A dermatoscopic image of a skin lesion.
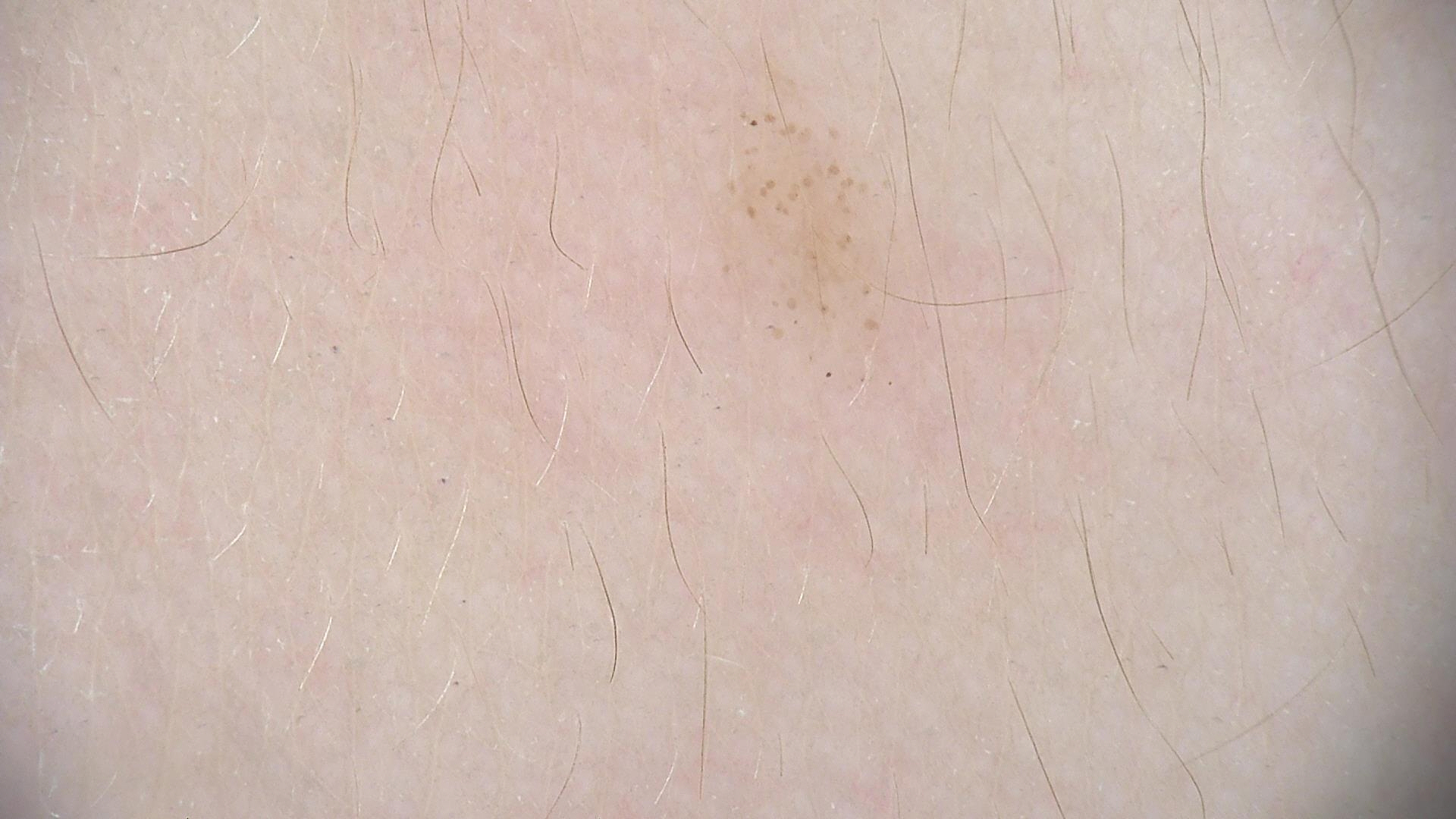Labeled as a benign lesion — a dysplastic junctional nevus.